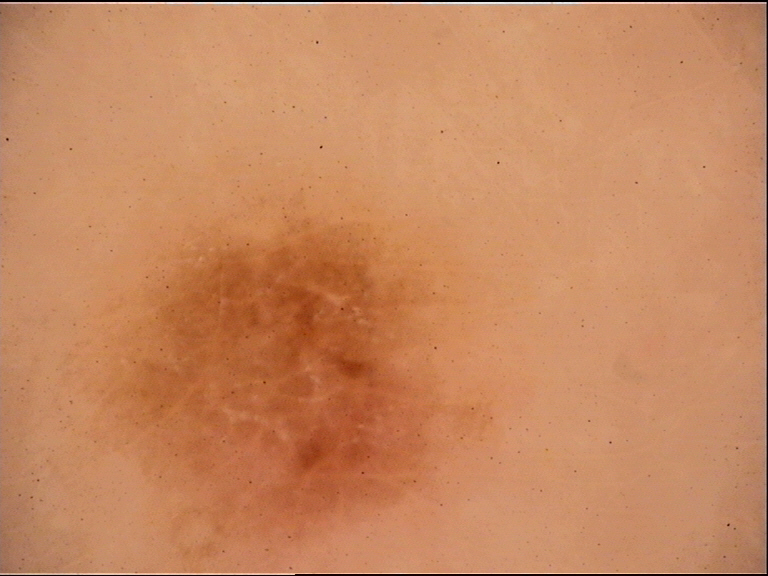A dermoscopic image of a skin lesion.
The diagnostic label was a banal lesion — a junctional nevus.